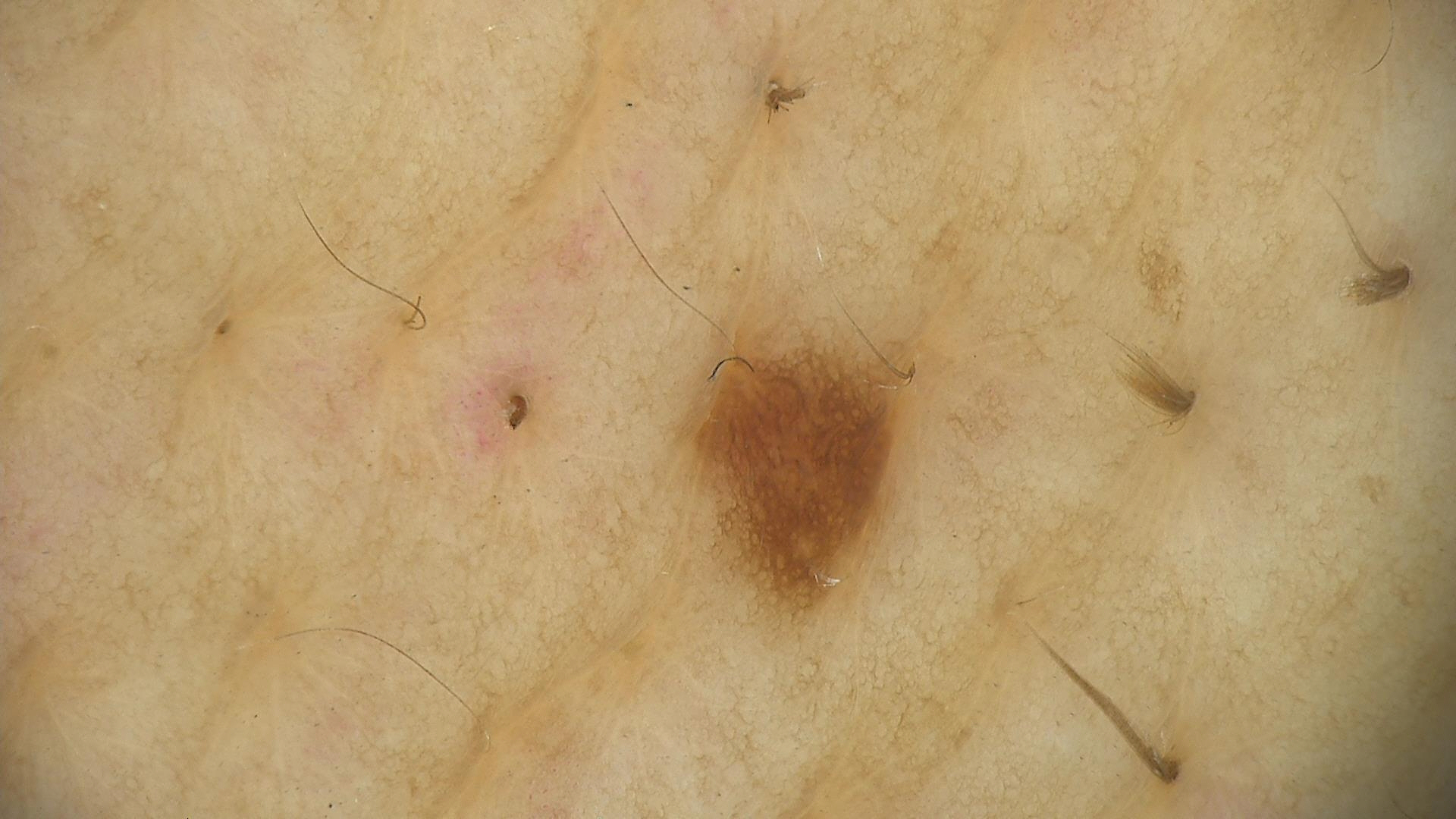{"image": "dermoscopy", "diagnosis": {"name": "dysplastic junctional nevus", "code": "jd", "malignancy": "benign", "super_class": "melanocytic", "confirmation": "expert consensus"}}